A dermoscopic image of a skin lesion. A female patient aged 68. Imaged for a research study, with no referral diagnosis recorded:
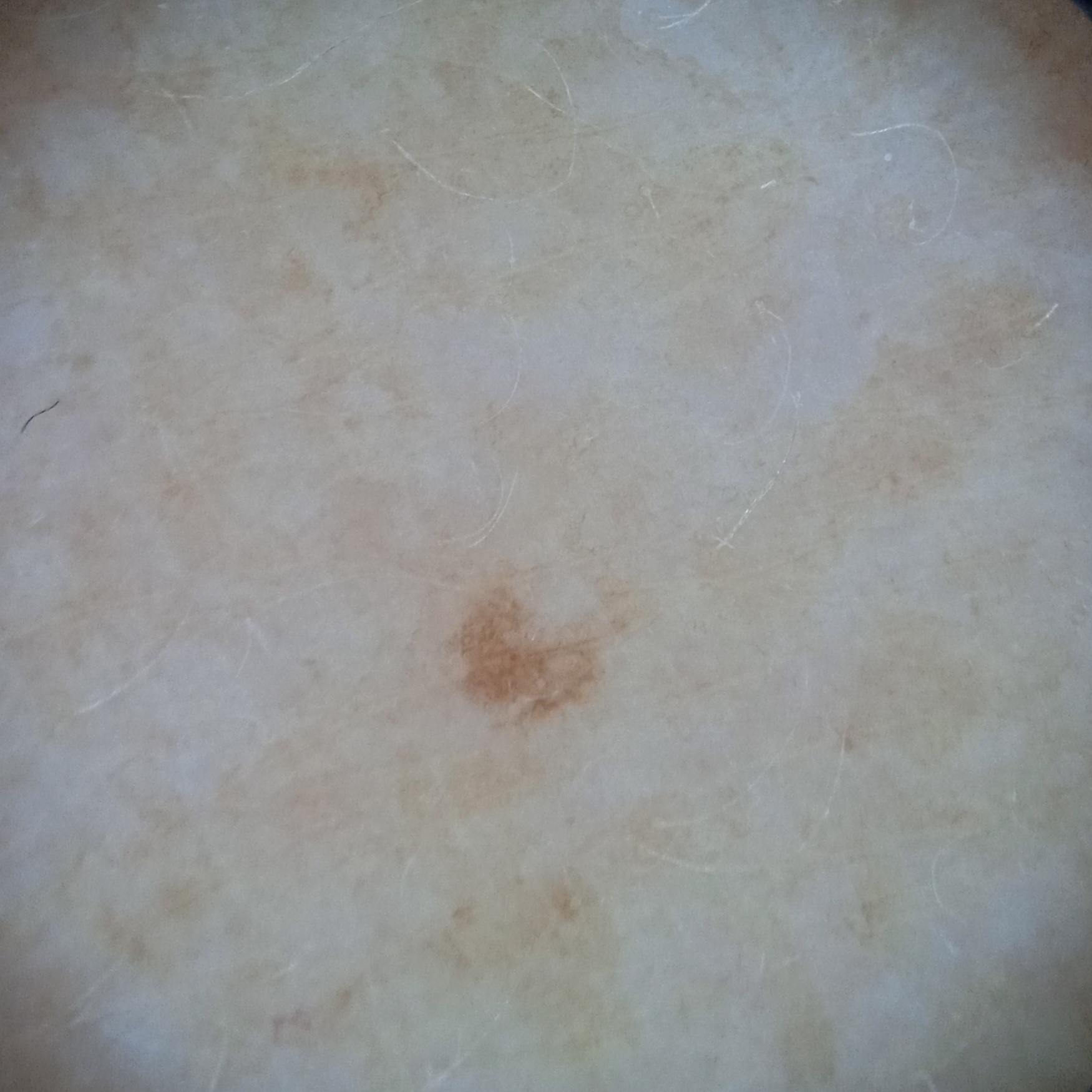The lesion measures approximately 1.7 mm.
The diagnostic impression was a melanocytic nevus.